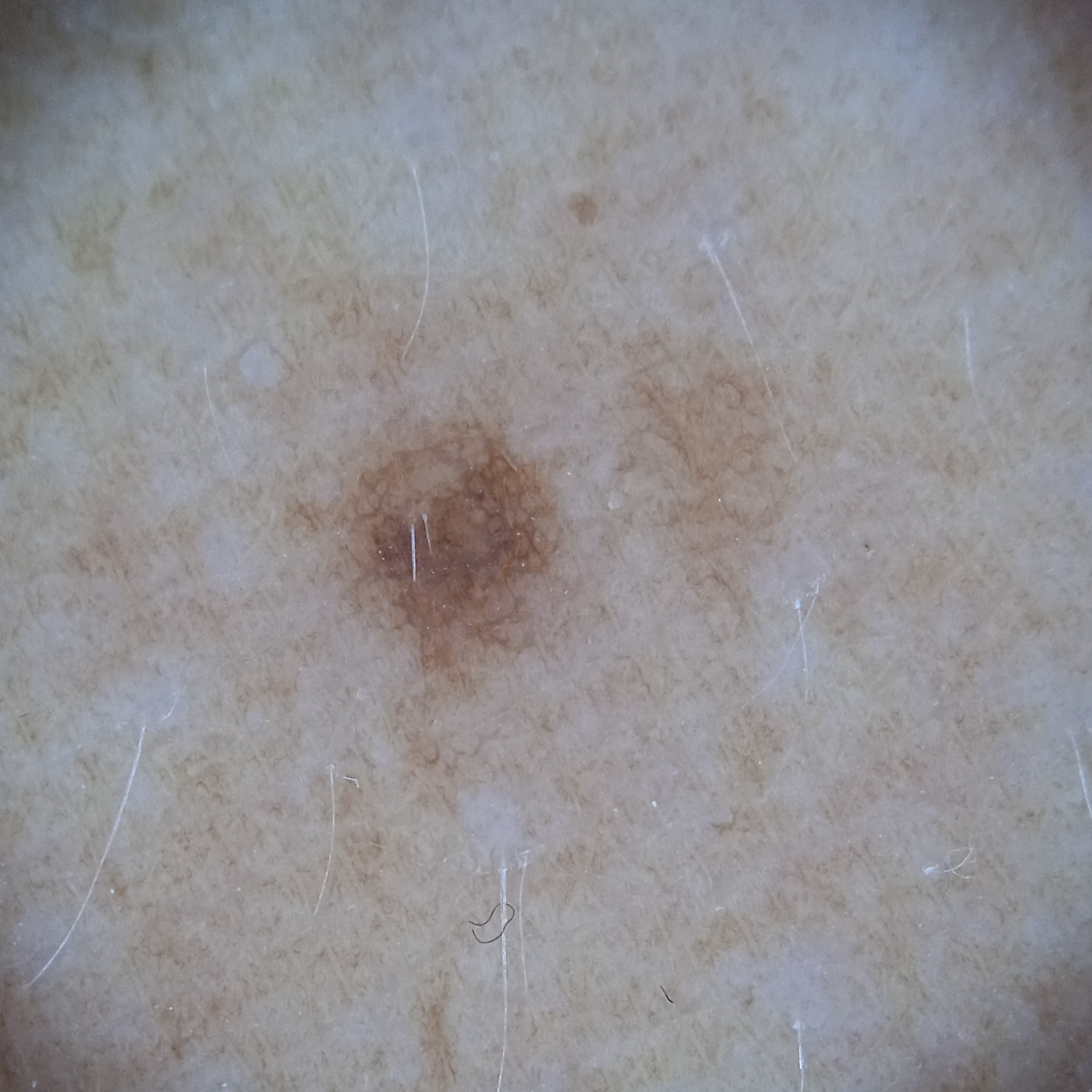A skin lesion imaged with a dermatoscope.
A male subject age 54.
The lesion is on an arm.
Measuring roughly 2.9 mm.
The four-dermatologist consensus diagnosis was a melanocytic nevus; the four reviewers were unanimous; diagnostic confidence was good.